A dermoscopic photograph of a skin lesion:
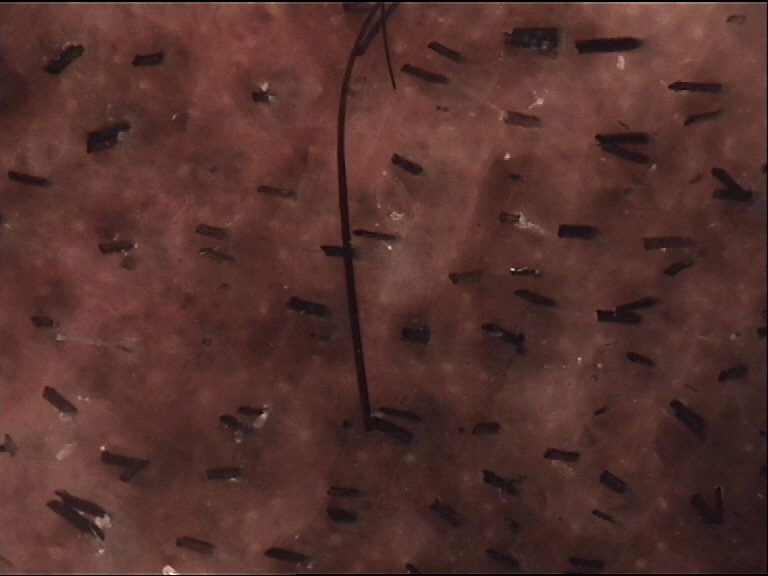lesion type = banal; diagnosis = congenital compound nevus (expert consensus).